A dermoscopic photograph of a skin lesion.
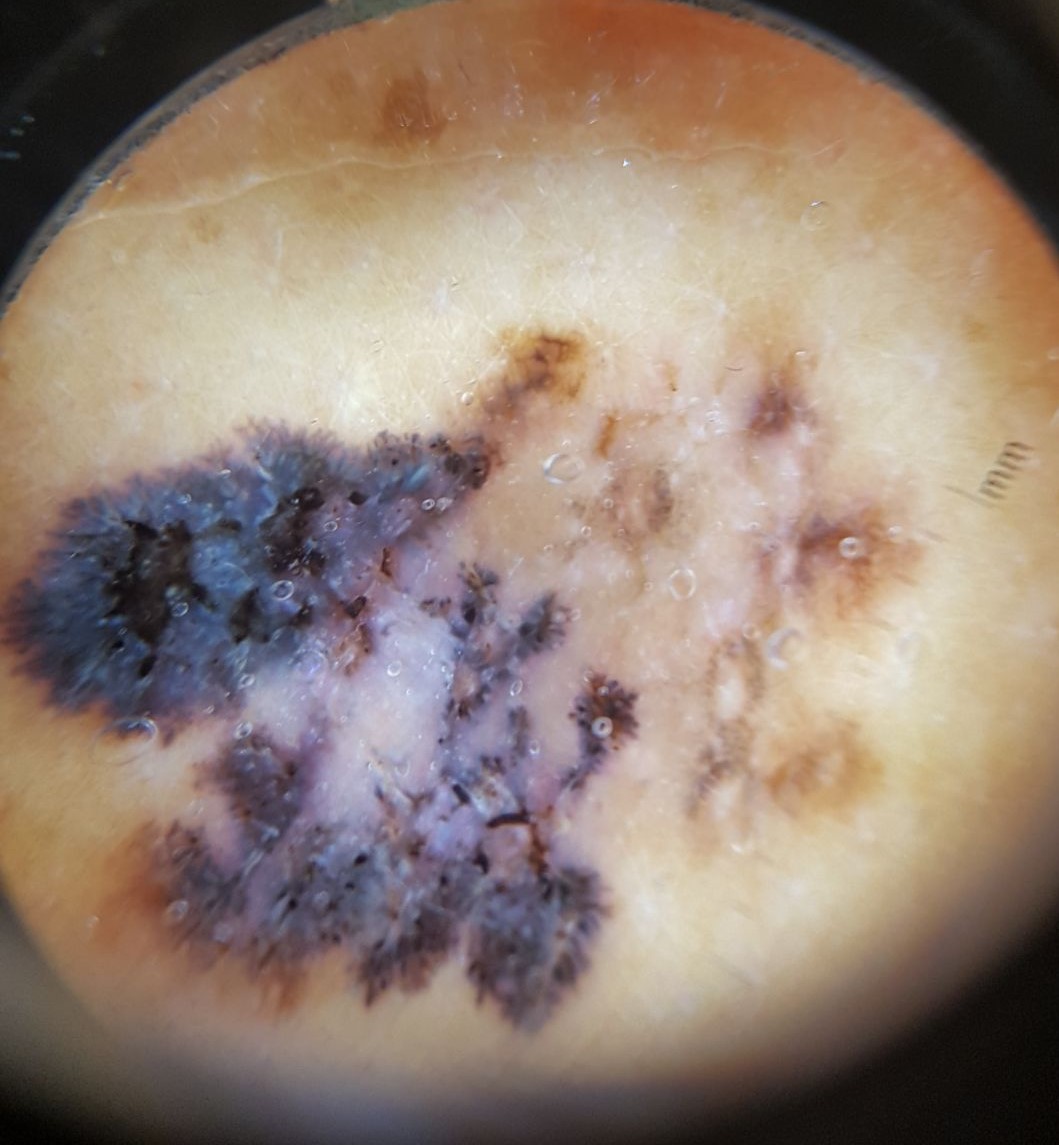{
  "diagnosis": {
    "name": "melanoma",
    "code": "mel",
    "malignancy": "malignant",
    "super_class": "melanocytic",
    "confirmation": "histopathology"
  }
}